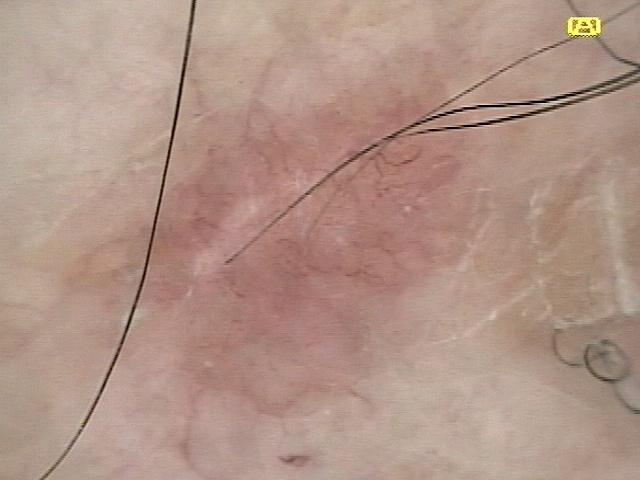subject=male, aged 83 or over; melanoma history=a prior melanoma; diagnosis=Basal cell carcinoma (biopsy-proven).